A male patient in their 80s. The patient is skin type II.
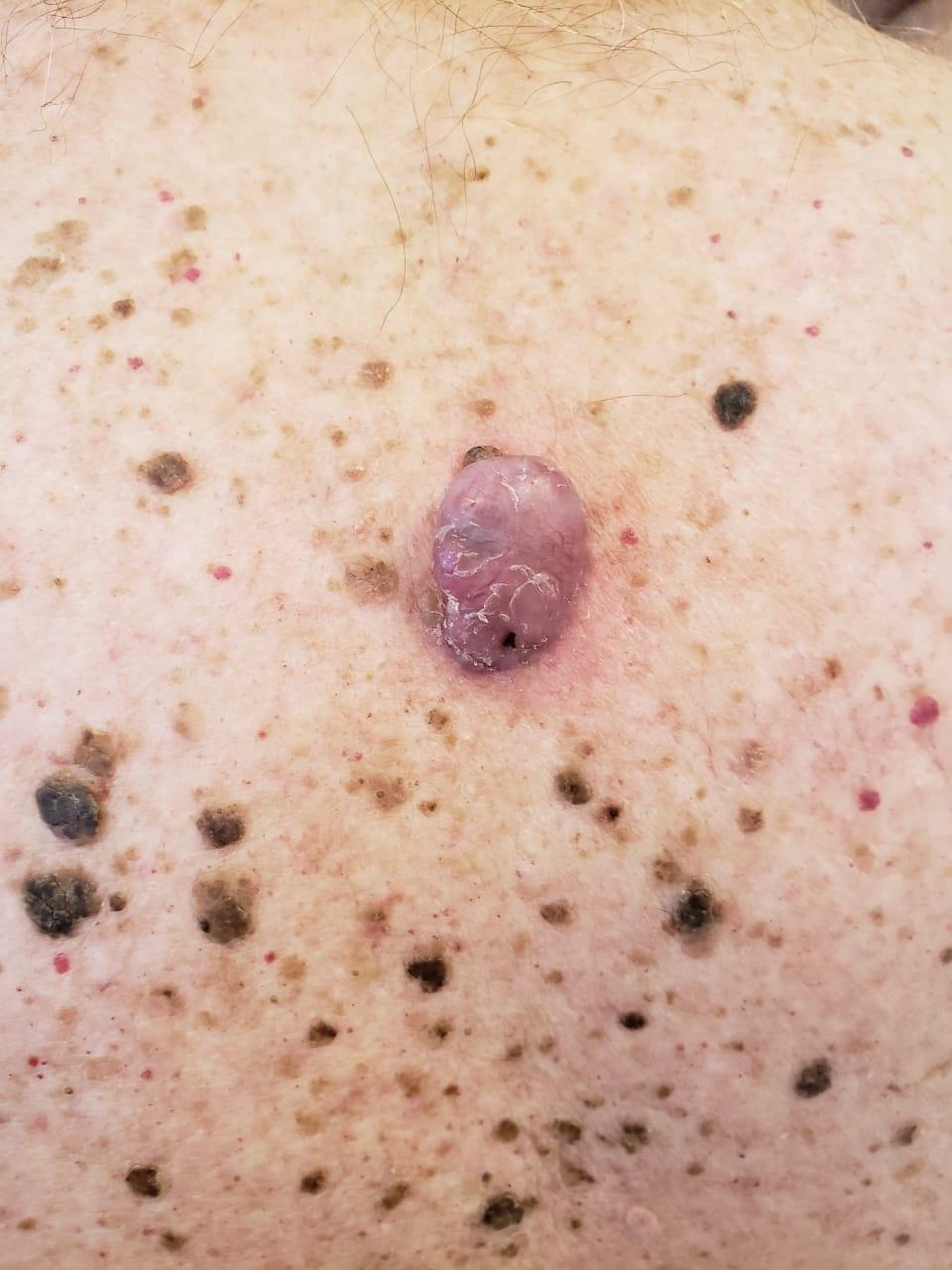<skin_lesion>
  <lesion_location>
    <region>the trunk</region>
    <detail>the posterior trunk</detail>
  </lesion_location>
  <diagnosis>
    <name>Melanoma</name>
    <malignancy>malignant</malignancy>
    <confirmation>histopathology</confirmation>
  </diagnosis>
</skin_lesion>